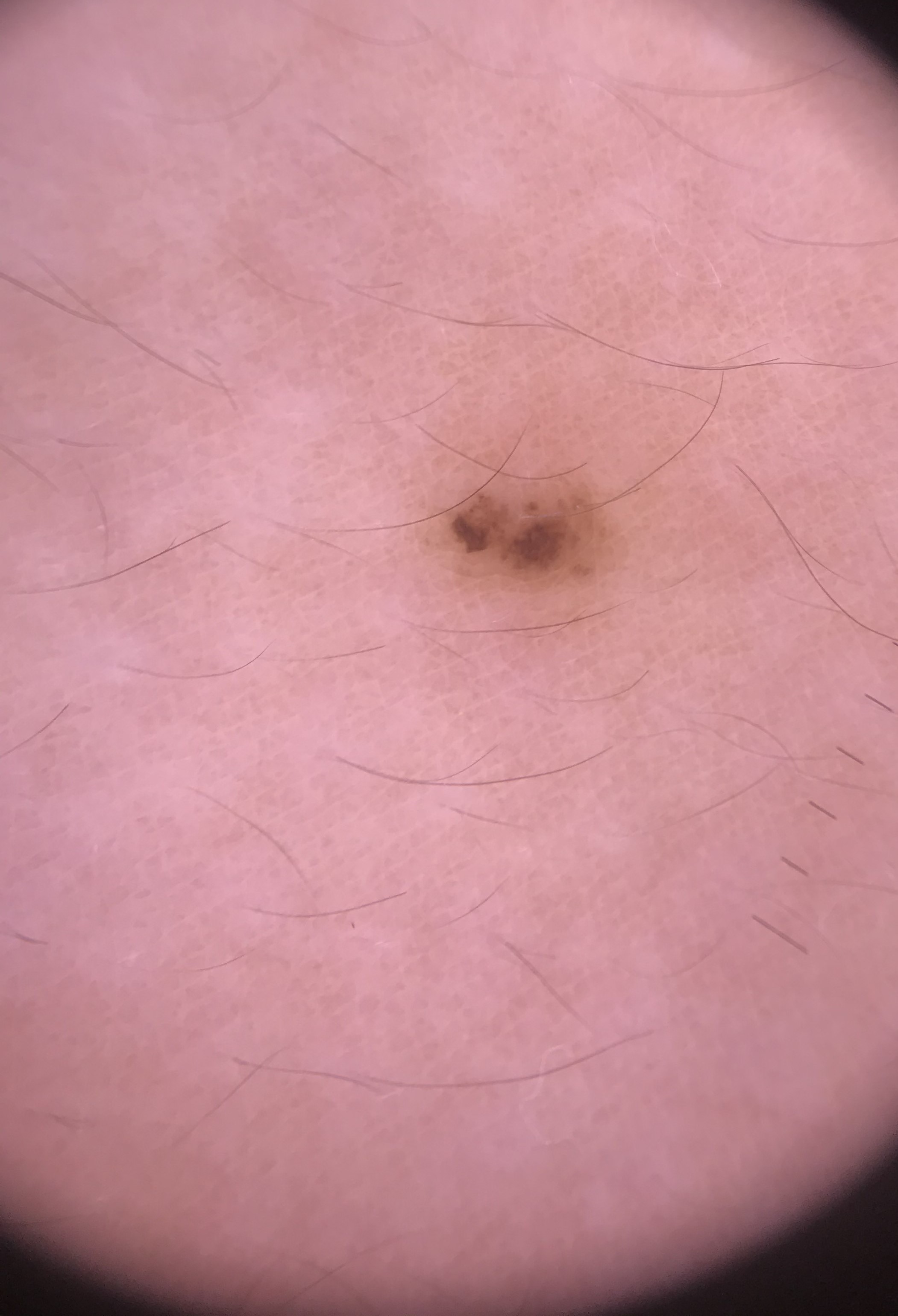Summary:
A dermoscopy image of a single skin lesion. The architecture is that of a banal lesion.
Impression:
The diagnostic label was a compound nevus.